The contributor is 18–29, male; an image taken at an angle — 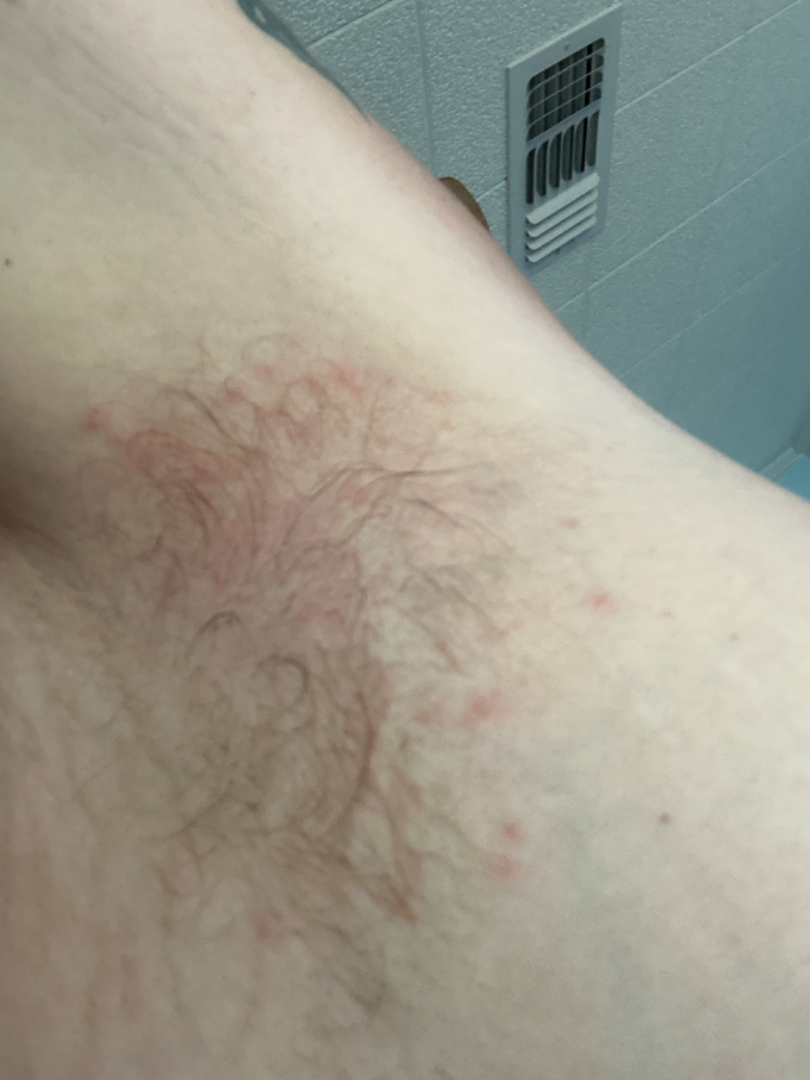dermatologist impression = the differential is split between Intertrigo and Seborrheic Dermatitis; a remote consideration is Folliculitis.